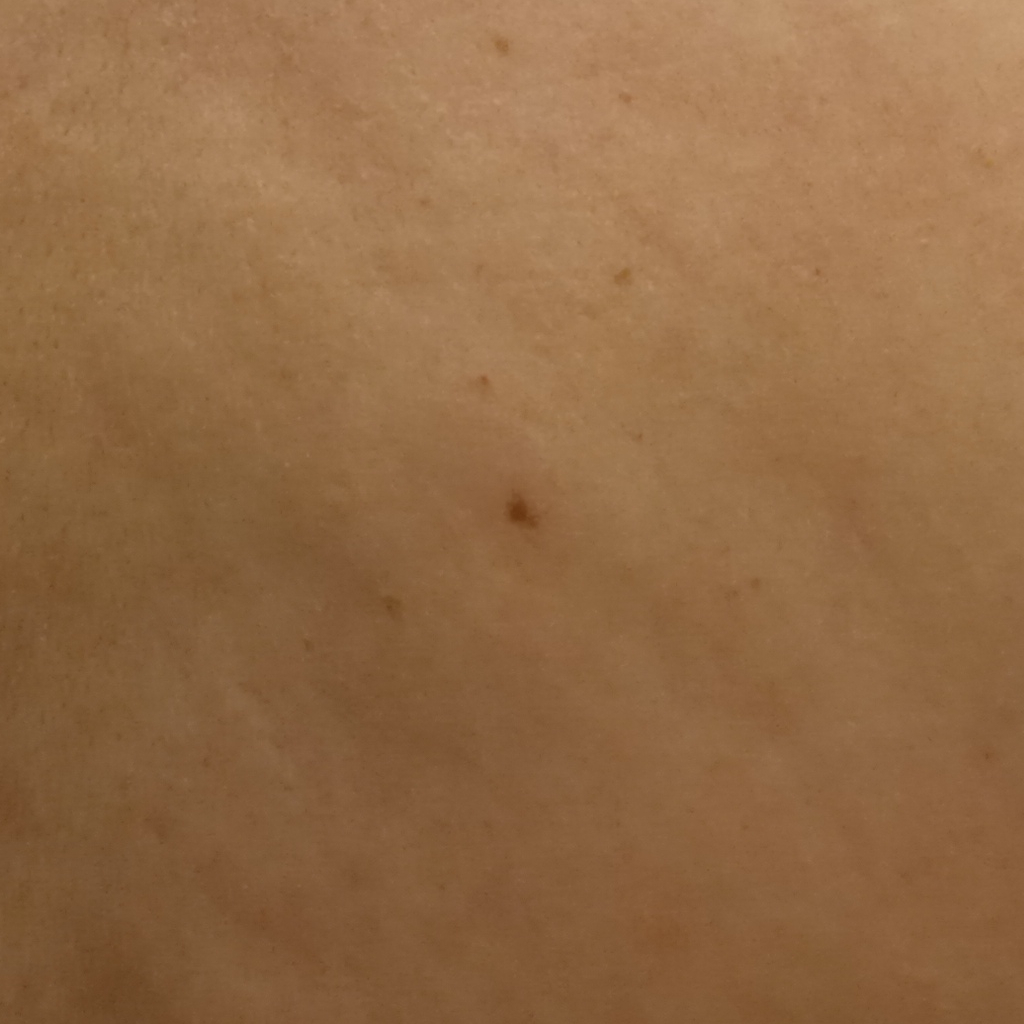<case>
  <image>clinical photograph</image>
  <patient>
    <age>48</age>
    <sex>female</sex>
  </patient>
  <lesion_location>the back</lesion_location>
  <lesion_size>
    <diameter_mm>3.7</diameter_mm>
  </lesion_size>
  <diagnosis>
    <name>melanocytic nevus</name>
    <malignancy>benign</malignancy>
  </diagnosis>
</case>